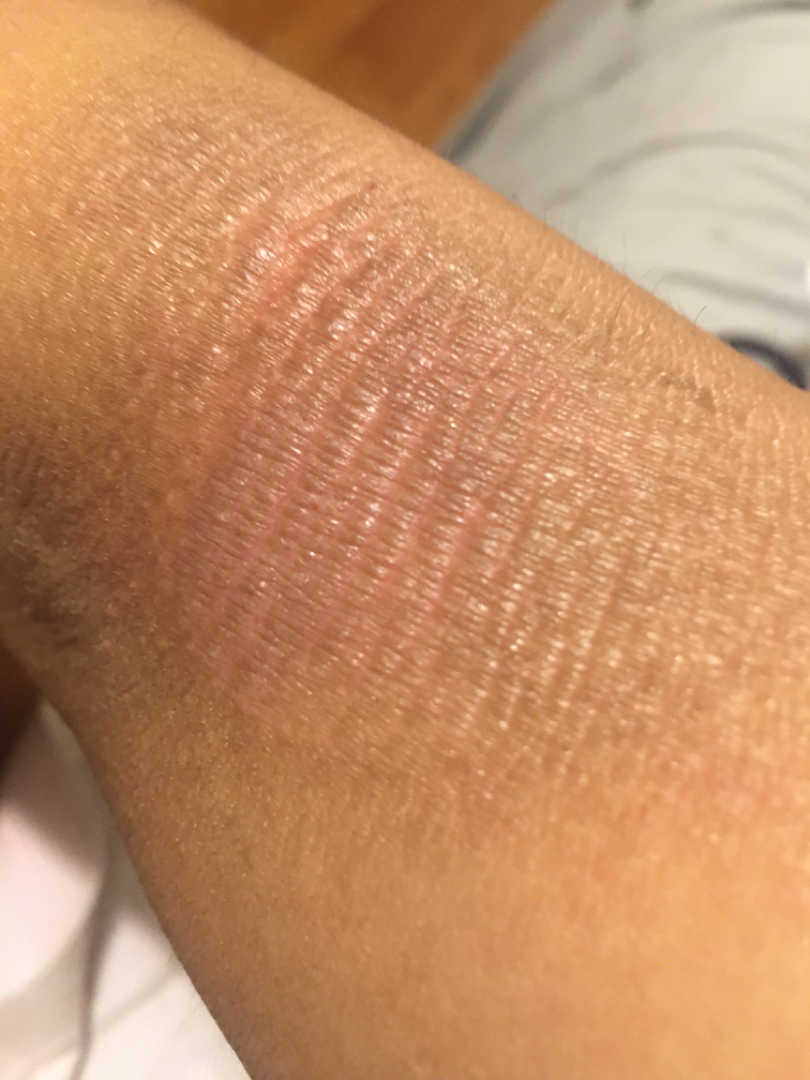Q: Who is the patient?
A: female, age 18–29
Q: What is the lesion texture?
A: rough or flaky
Q: Where on the body?
A: arm
Q: Reported symptoms?
A: darkening, burning and itching
Q: Duration?
A: three to twelve months
Q: Any systemic symptoms?
A: none reported
Q: How was the photo taken?
A: close-up
Q: What conditions are considered?
A: Lichen Simplex Chronicus, Lichen planus/lichenoid eruption and Eczema were each considered, in no particular order